A male patient, aged 33 to 37 · a skin lesion imaged with a dermatoscope: 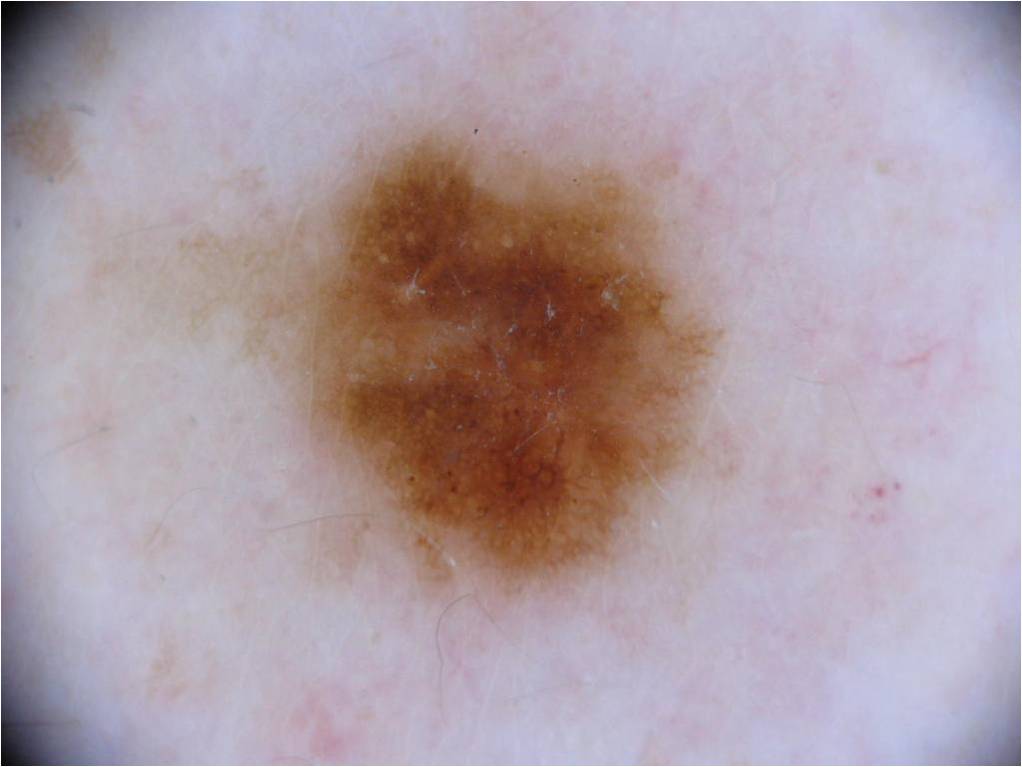Findings:
– bounding box: [176,108,725,617]
– dermoscopic features: globules and pigment network
– diagnosis: a melanocytic nevus